The patient says their skin reddens with sun exposure. A male subject aged 72. Collected as part of a research study, without a referral diagnosis. Few moles overall by the patient's own estimate. A clinical close-up of a skin lesion. On a questionnaire the patient reported a personal history of cancer and no immunosuppression — 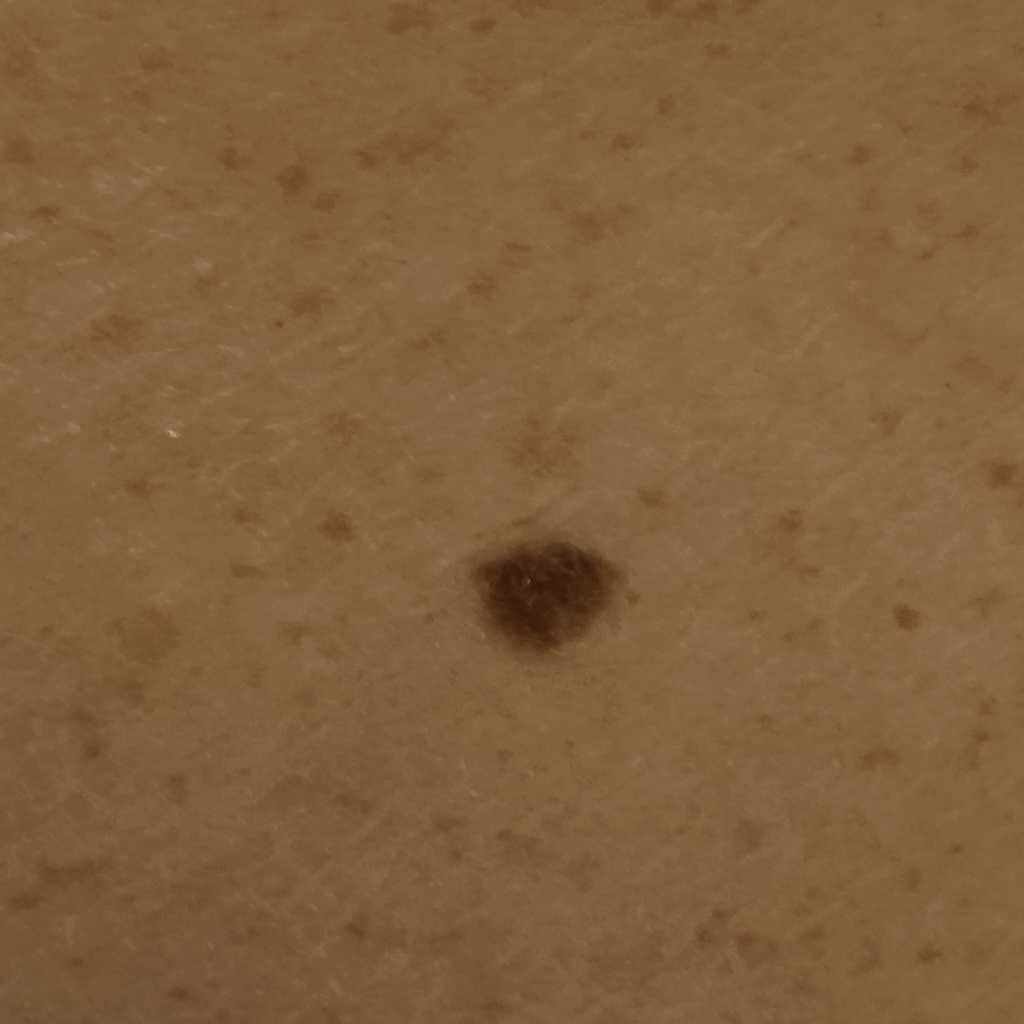Located on the back. The diagnostic impression was a melanocytic nevus.